A dermoscopic image of a skin lesion.
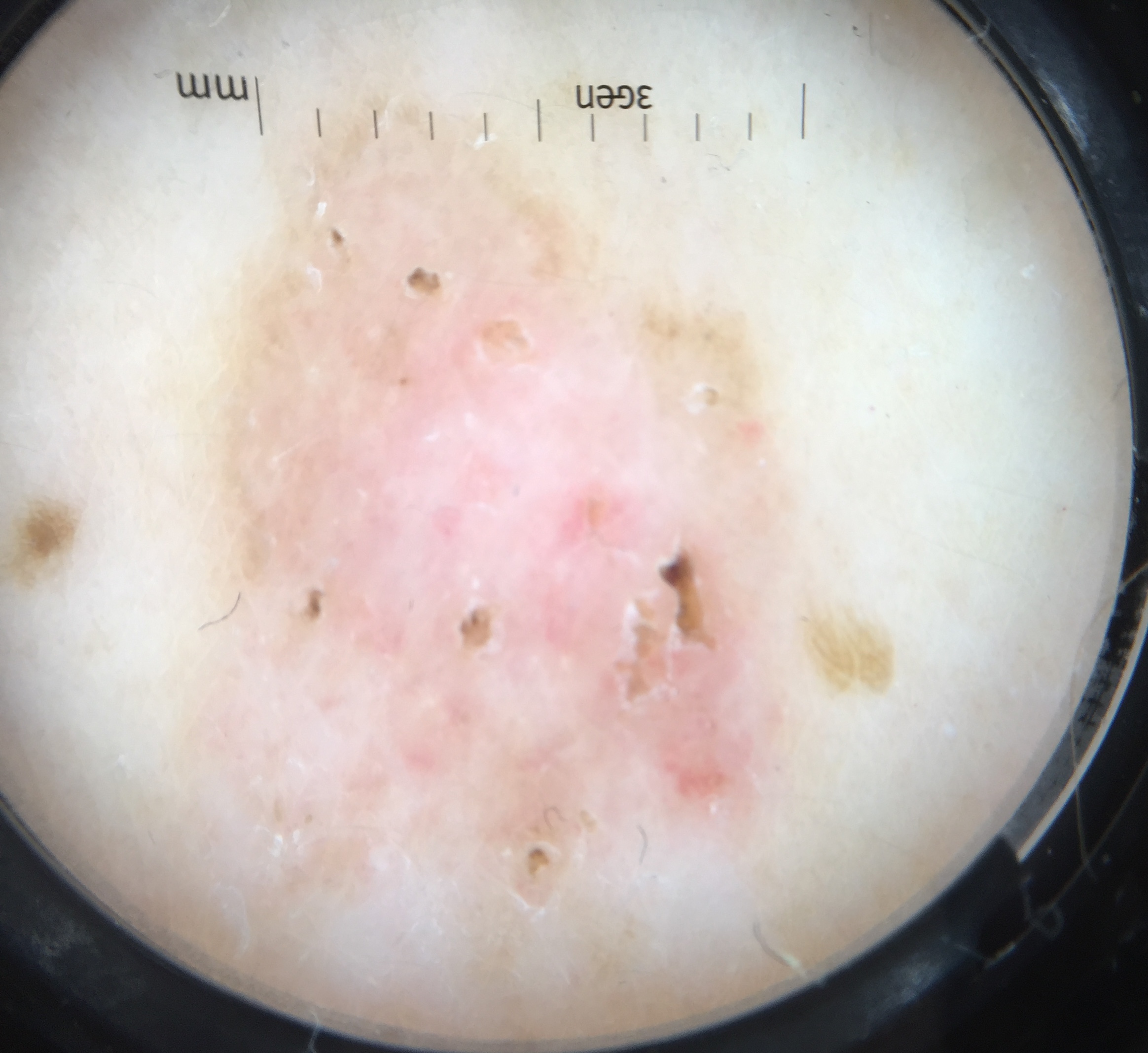| feature | finding |
|---|---|
| class | basal cell carcinoma (biopsy-proven) |